The lesion is described as flat · the patient notes the condition has been present for less than one week · the patient described the issue as skin that appeared healthy to them · the photograph is a close-up of the affected area · no associated lesion symptoms were reported · no constitutional symptoms were reported · the leg is involved — 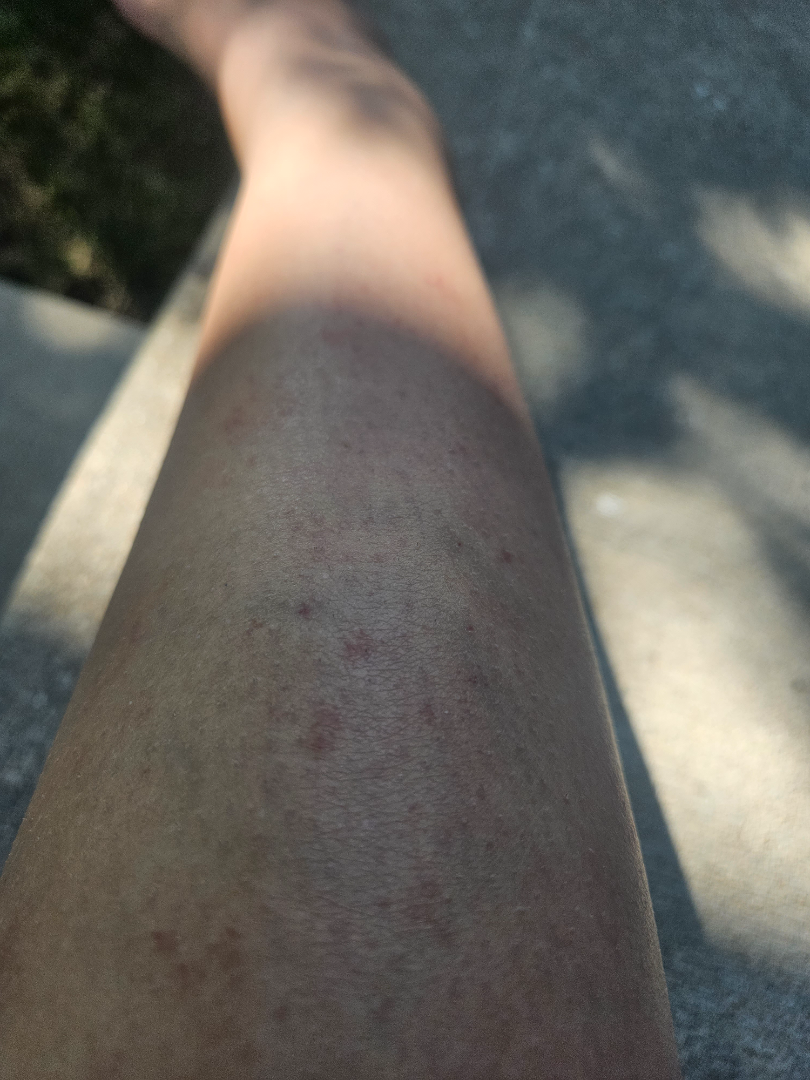assessment = not assessable.